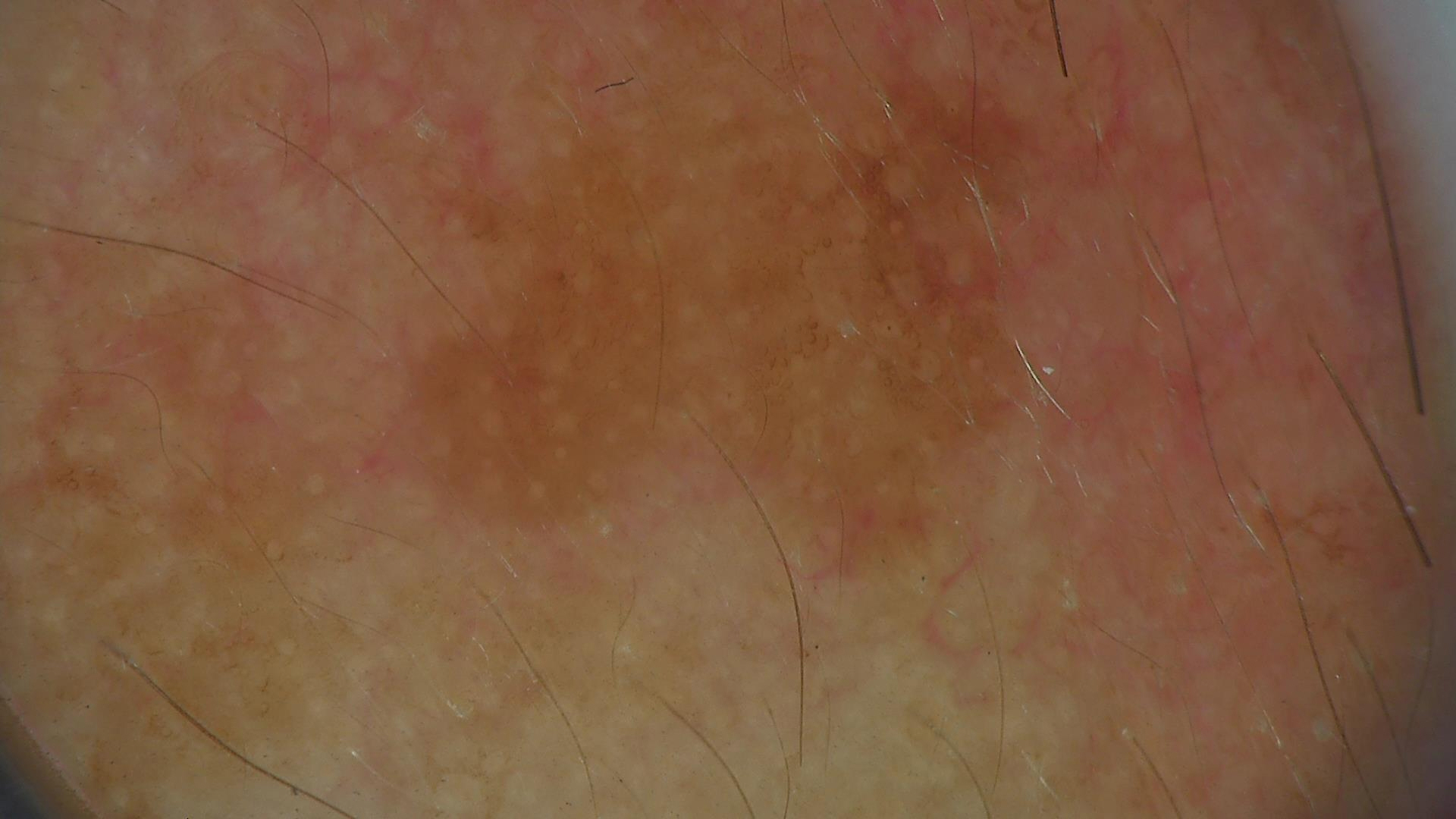The architecture is that of a keratinocytic lesion. The diagnostic label was a benign lesion — a seborrheic keratosis.